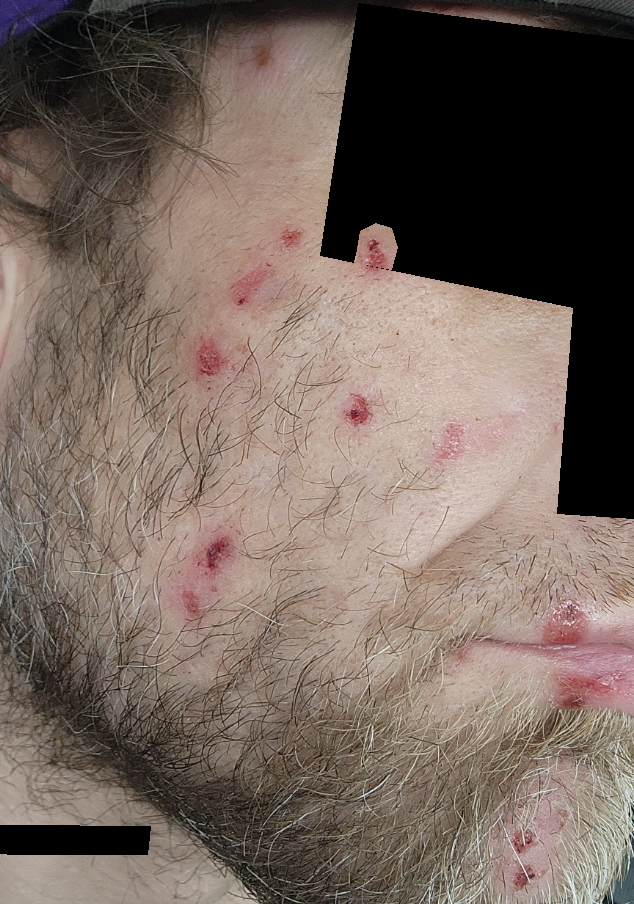Review:
The primary impression is Inflicted skin lesions; an alternative is Acne; a remote consideration is Bacterial pyoderma.